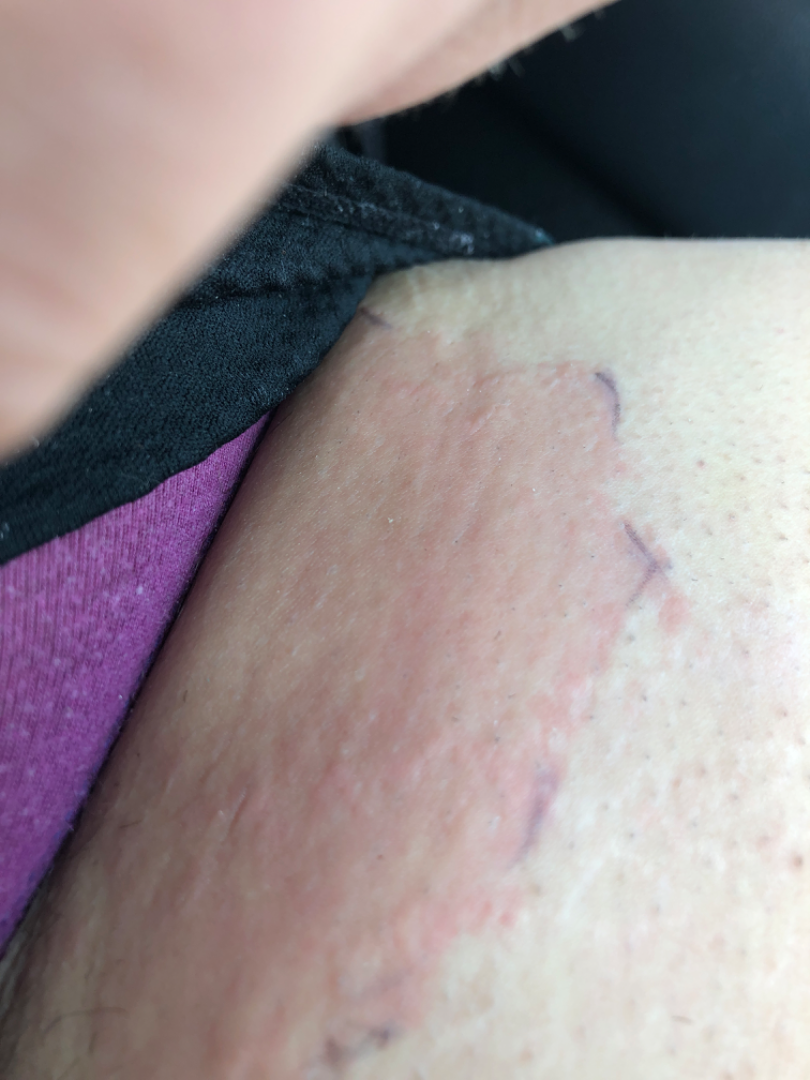Q: Constitutional symptoms?
A: none reported
Q: How long has this been present?
A: less than one week
Q: How does the patient describe it?
A: a rash
Q: What is the framing?
A: at an angle
Q: What symptoms does the patient report?
A: itching, enlargement and bothersome appearance
Q: Texture?
A: raised or bumpy
Q: What is the affected area?
A: leg
Q: What is the dermatologist's impression?
A: the differential is split between Cellulitis, Intertrigo and Psoriasis